A male subject, in their 70s · a skin lesion imaged with a dermatoscope.
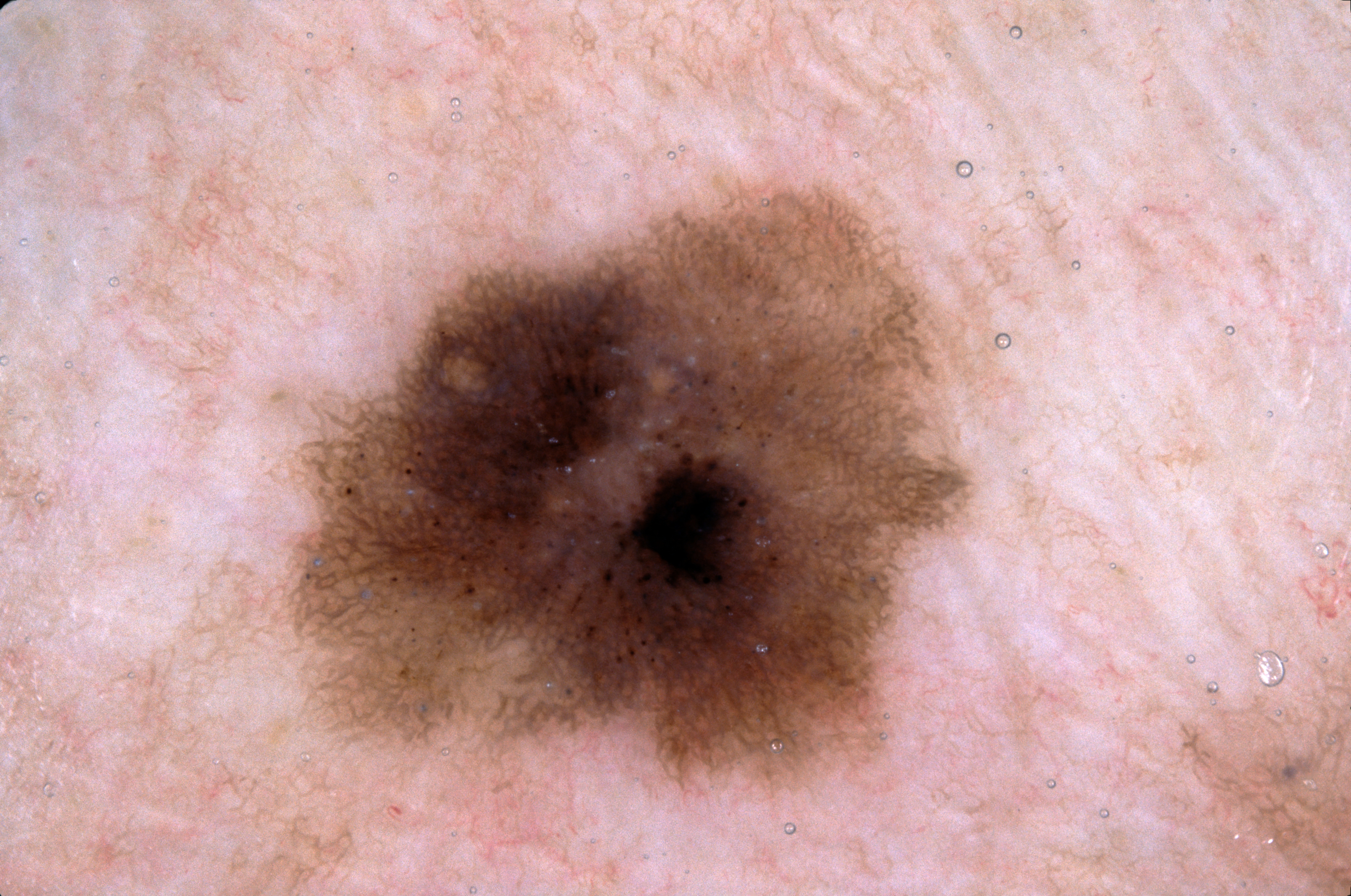With coordinates (x1, y1, x2, y2), lesion location: box(285, 189, 971, 784).
Dermoscopic examination shows pigment network.
Consistent with a melanocytic nevus.